The contributor is 50–59, female. The photograph is a close-up of the affected area. Located on the back of the hand, leg and arm: 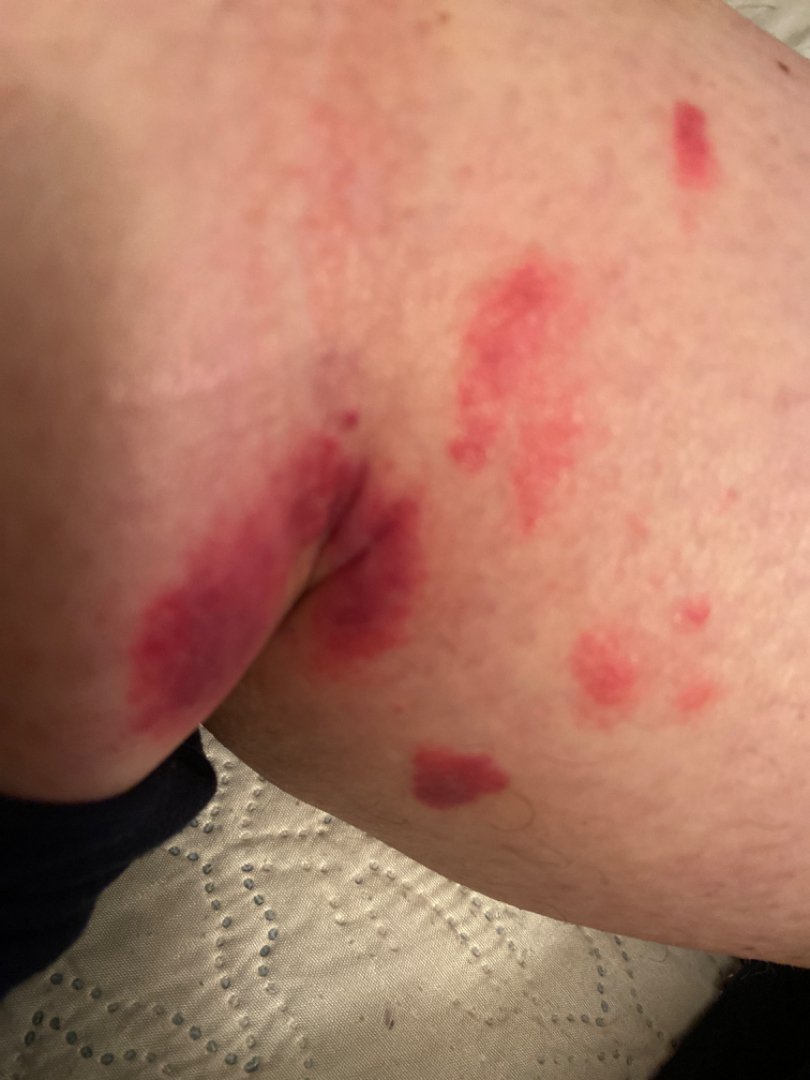assessment=indeterminate from the photograph | symptoms=itching, enlargement, darkening and bothersome appearance | described texture=rough or flaky and raised or bumpy | patient's own categorization=a rash | associated systemic symptoms=none reported.